A dermoscopy image of a single skin lesion.
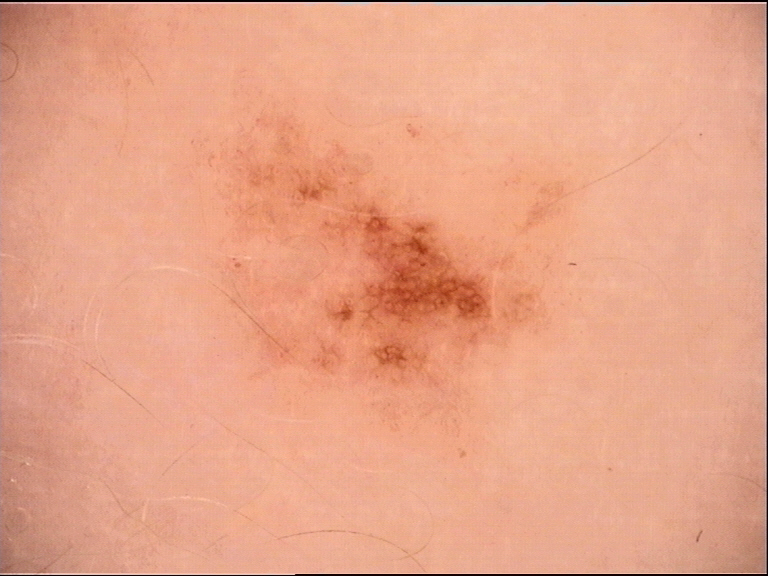| field | value |
|---|---|
| diagnostic label | dysplastic junctional nevus (expert consensus) |